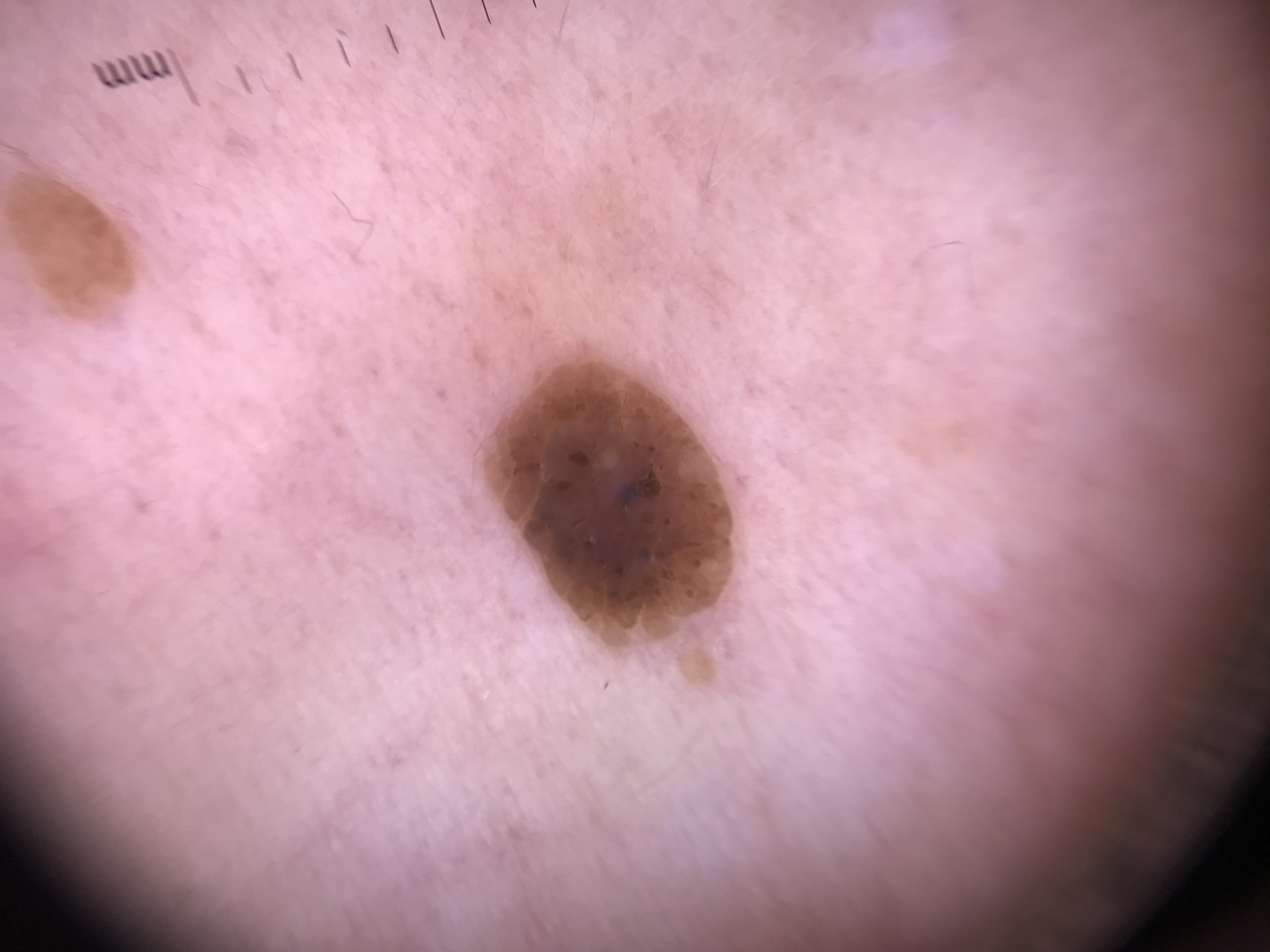The architecture is that of a keratinocytic lesion. Consistent with a seborrheic keratosis.